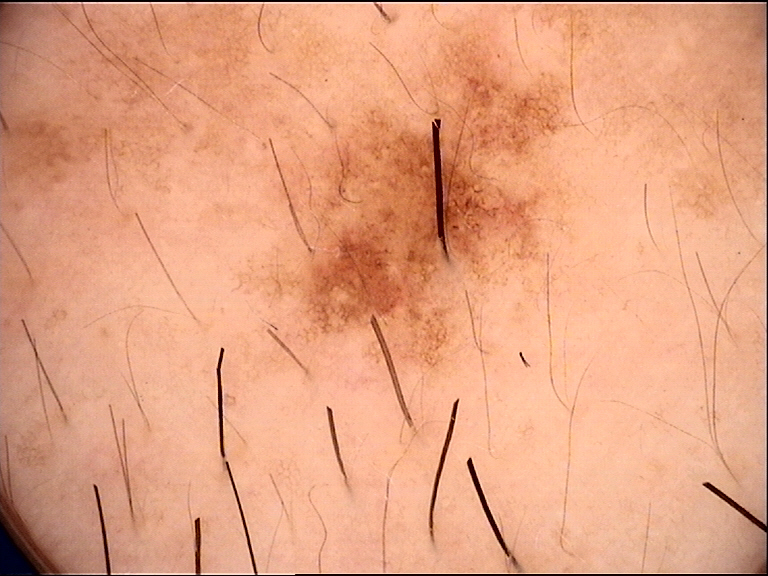{
  "image": "dermatoscopy",
  "diagnosis": {
    "name": "dysplastic junctional nevus",
    "code": "jd",
    "malignancy": "benign",
    "super_class": "melanocytic",
    "confirmation": "expert consensus"
  }
}